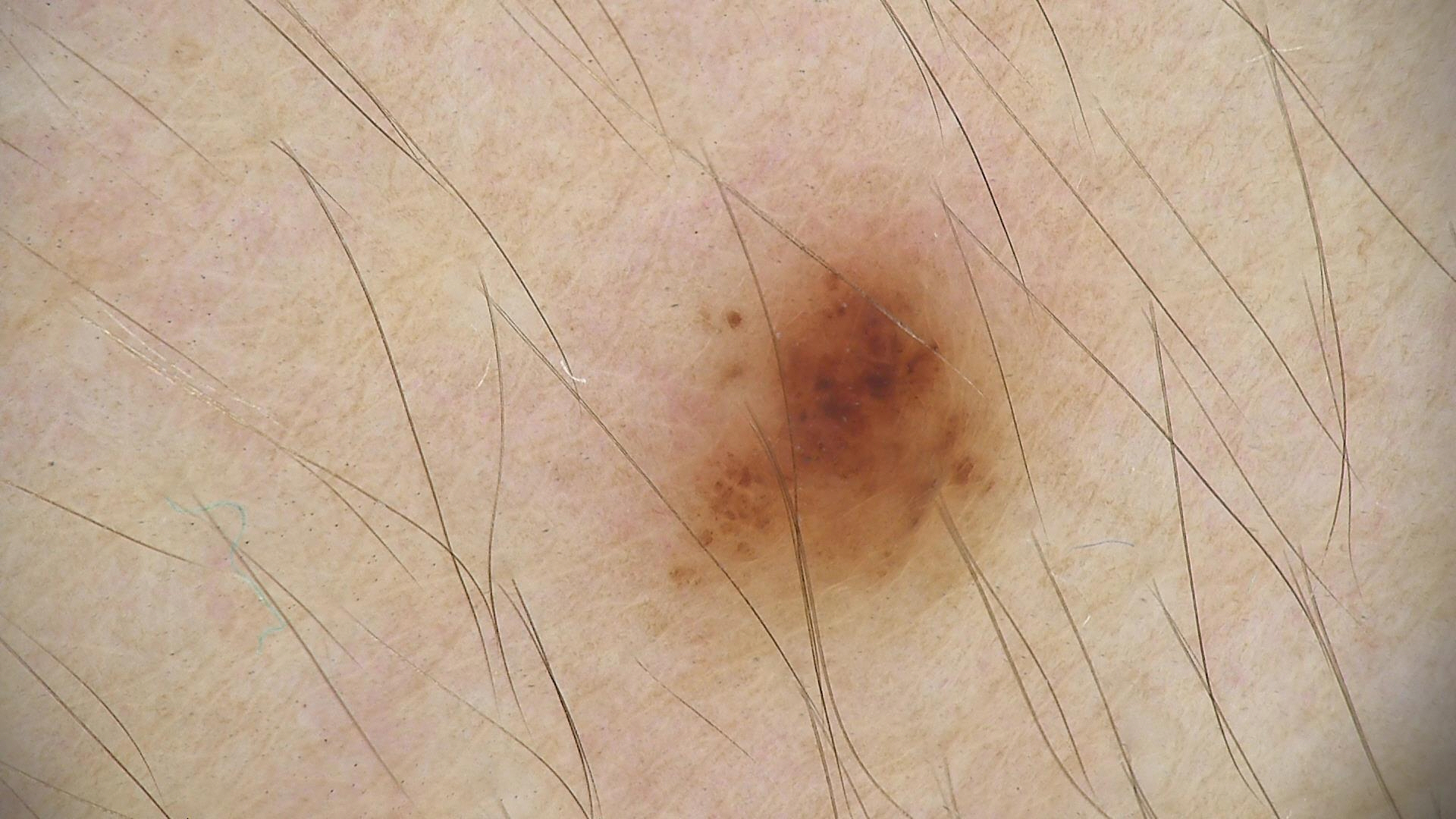A dermoscopic image of a skin lesion. The diagnosis was a dysplastic junctional nevus.